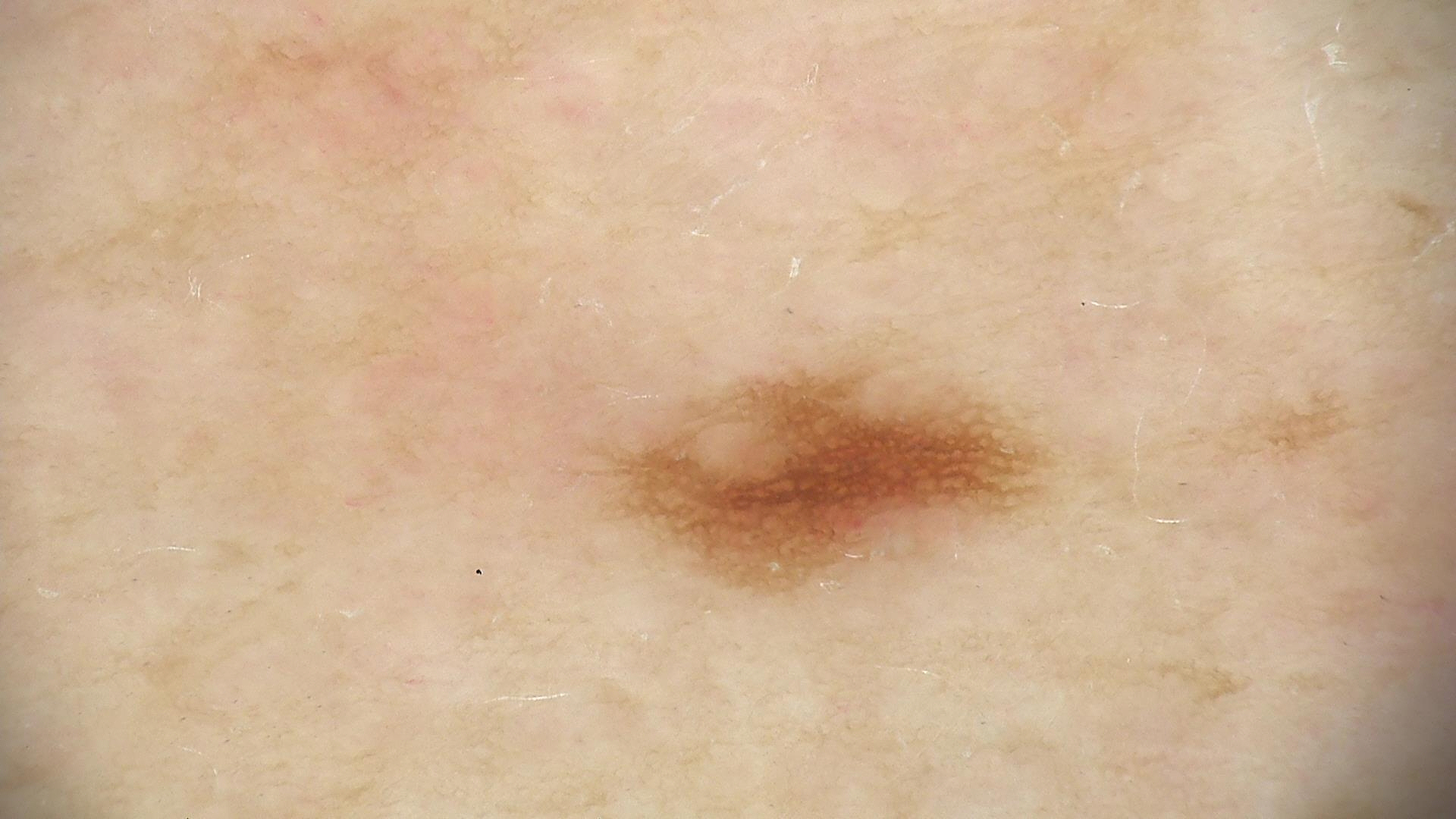Case:
A dermoscopy image of a single skin lesion.
Conclusion:
The diagnostic label was a benign lesion — a dysplastic junctional nevus.